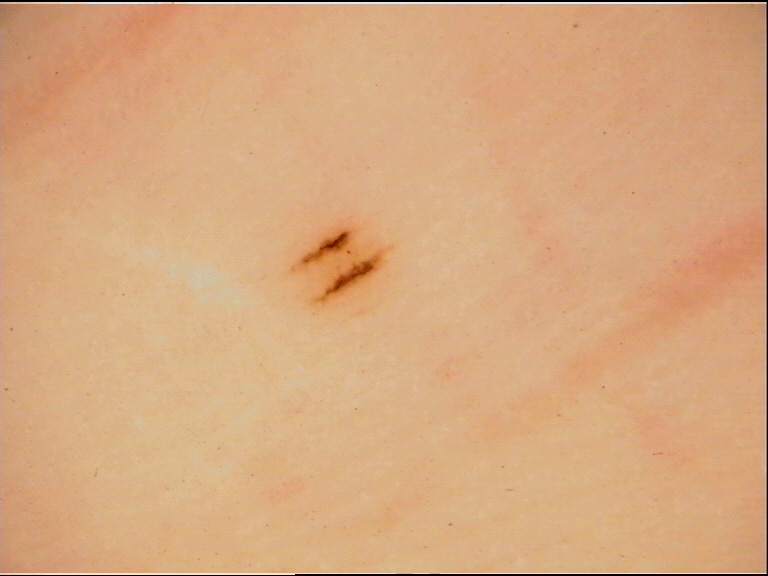This is a banal lesion. The diagnosis was an acral junctional nevus.